The lesion involves the arm. The photograph was taken at an angle. The contributor is a female aged 30–39.
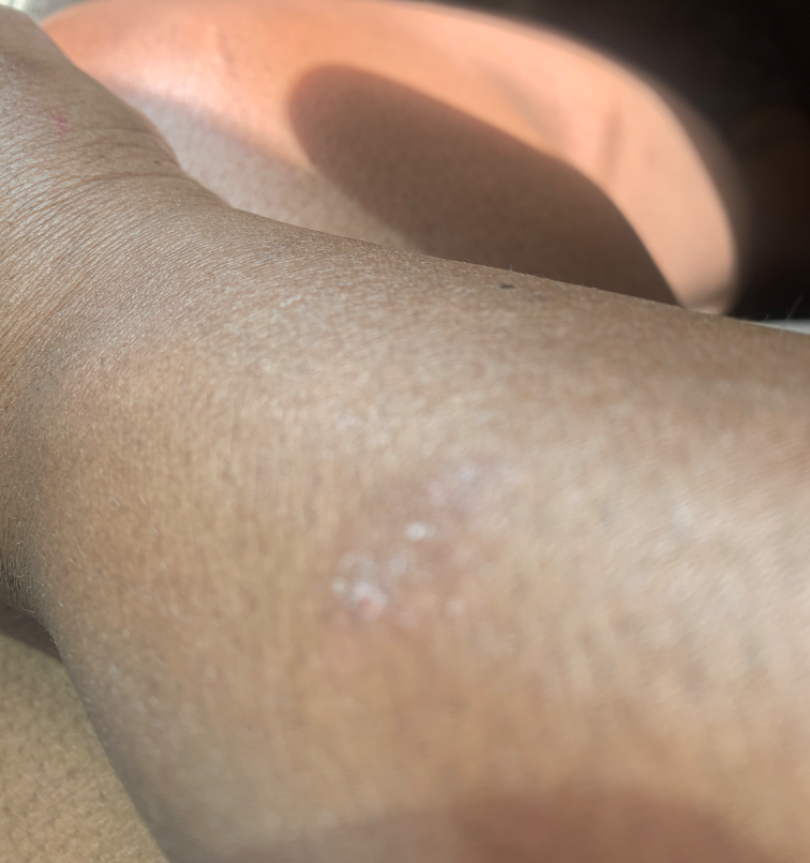Case summary:
• impression — the differential includes Psoriasis and Eczema, with no clear leading consideration